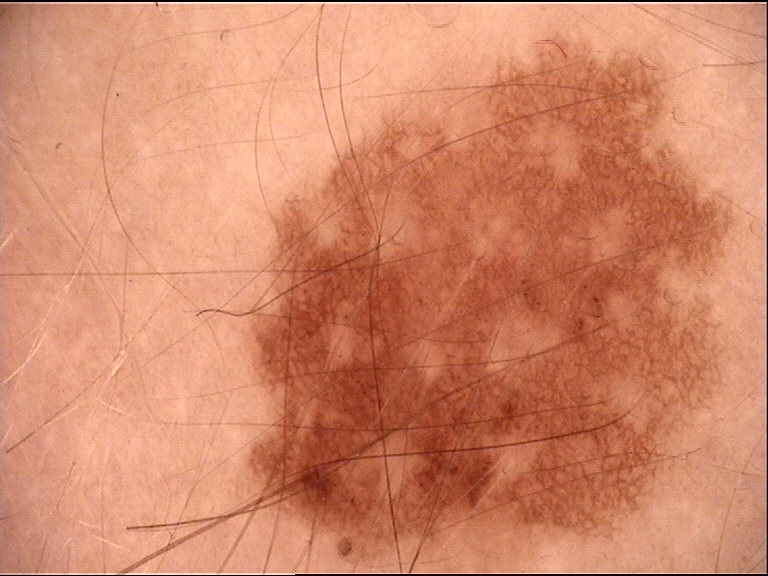The diagnosis was a congenital junctional nevus.